This is a close-up image · male subject, age 30–39 · the leg and top or side of the foot are involved:
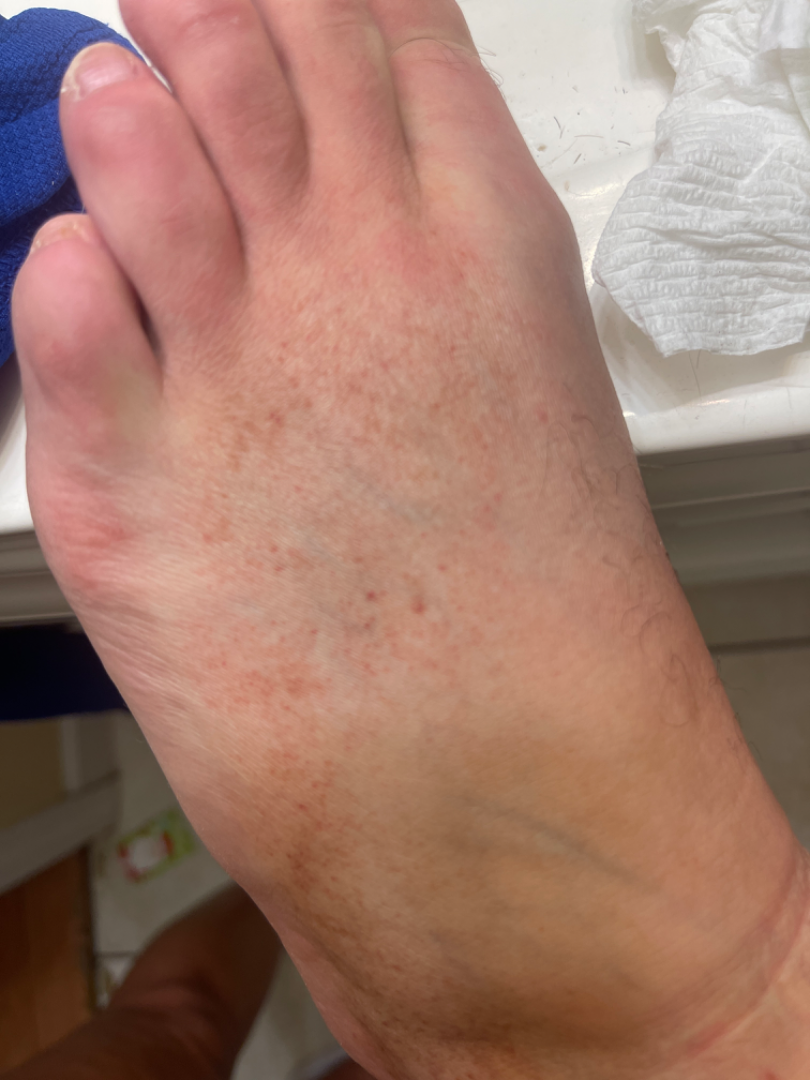Assessment:
A single dermatologist reviewed the case: most consistent with Pigmented purpuric eruption; an alternative is Stasis Dermatitis; the differential also includes Leukocytoclastic Vasculitis.